A dermoscopy image of a single skin lesion.
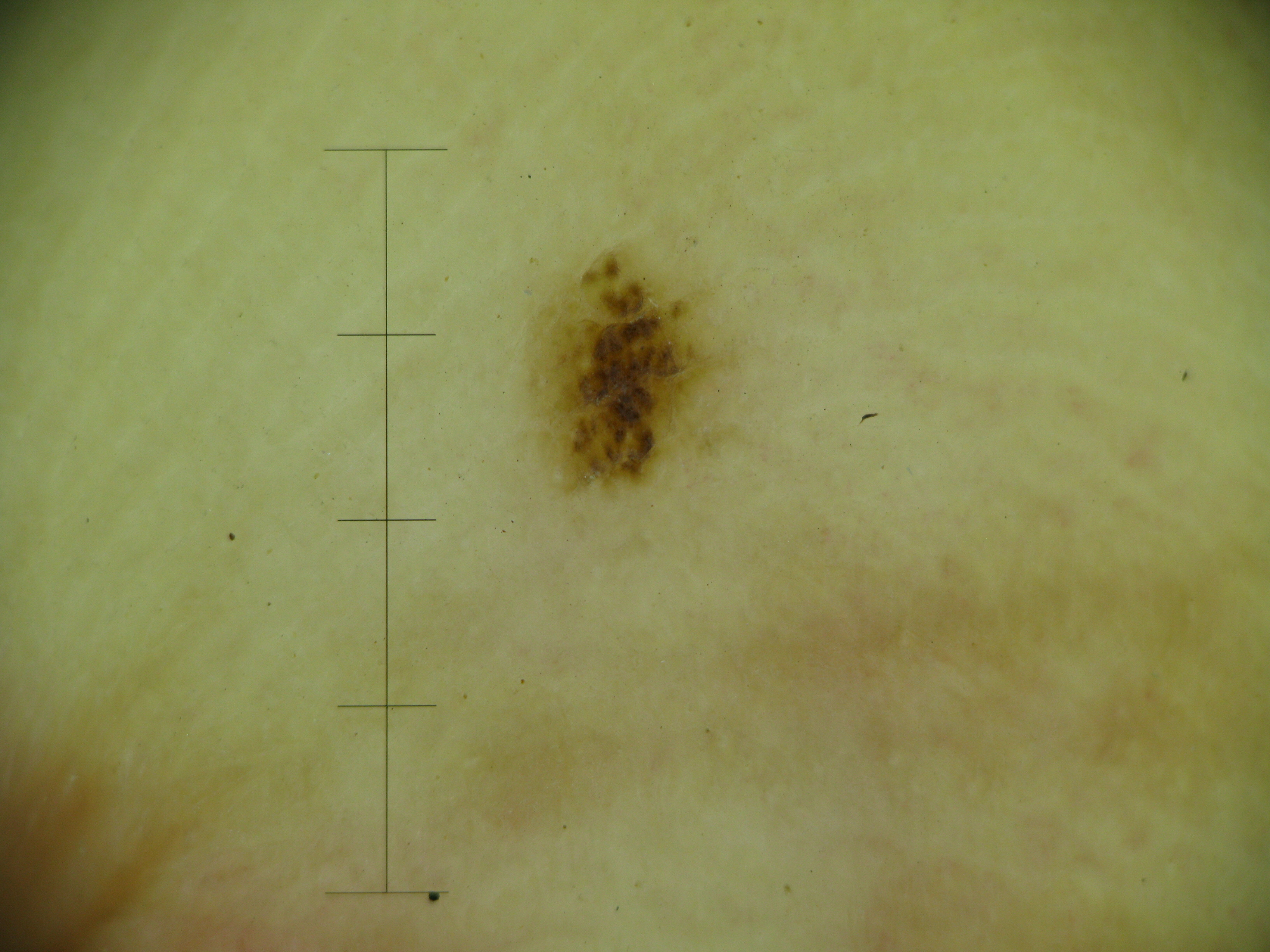Case:
* classification · banal
* diagnosis · acral compound nevus (expert consensus)